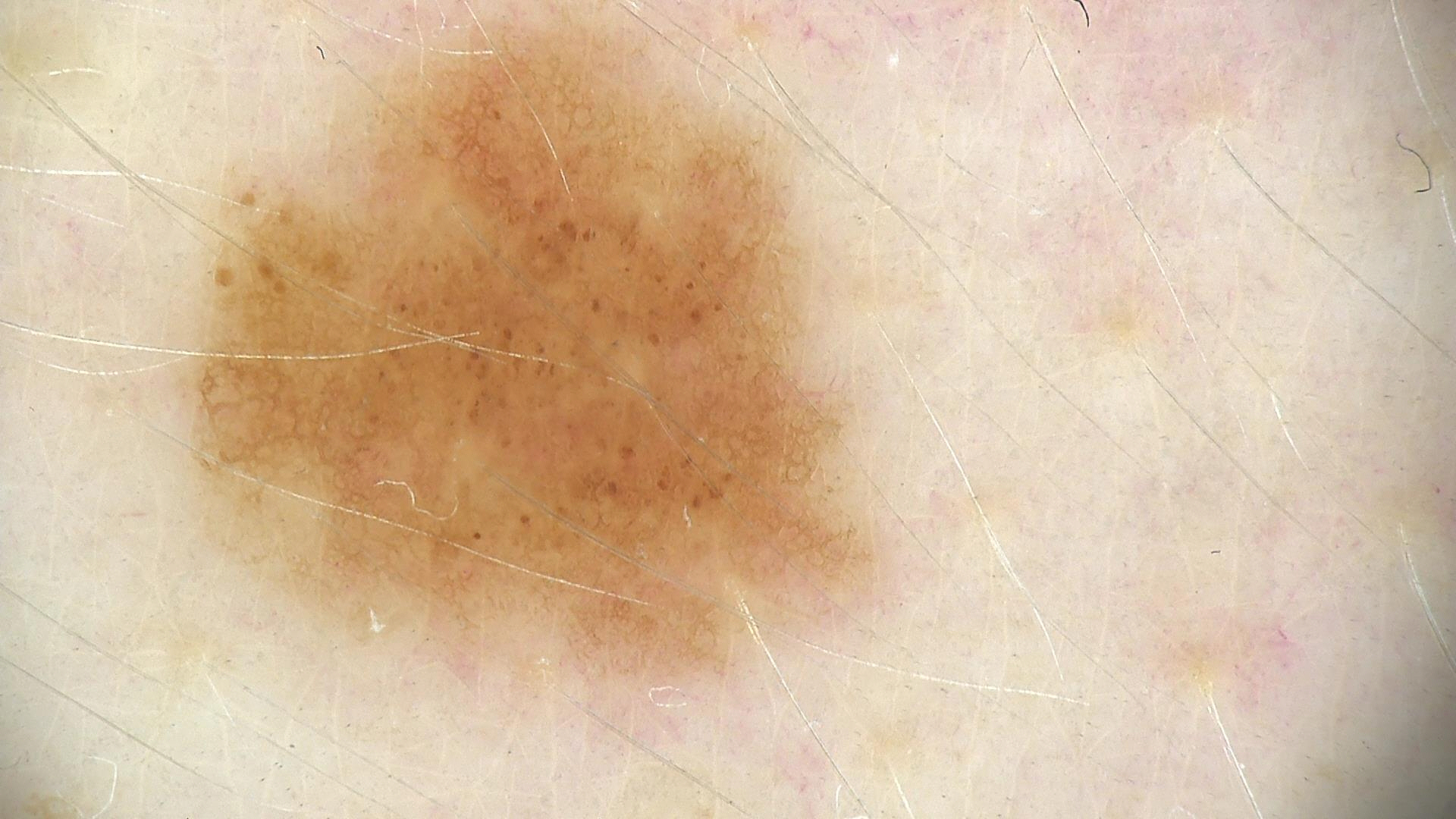Impression:
The diagnosis was a dysplastic junctional nevus.